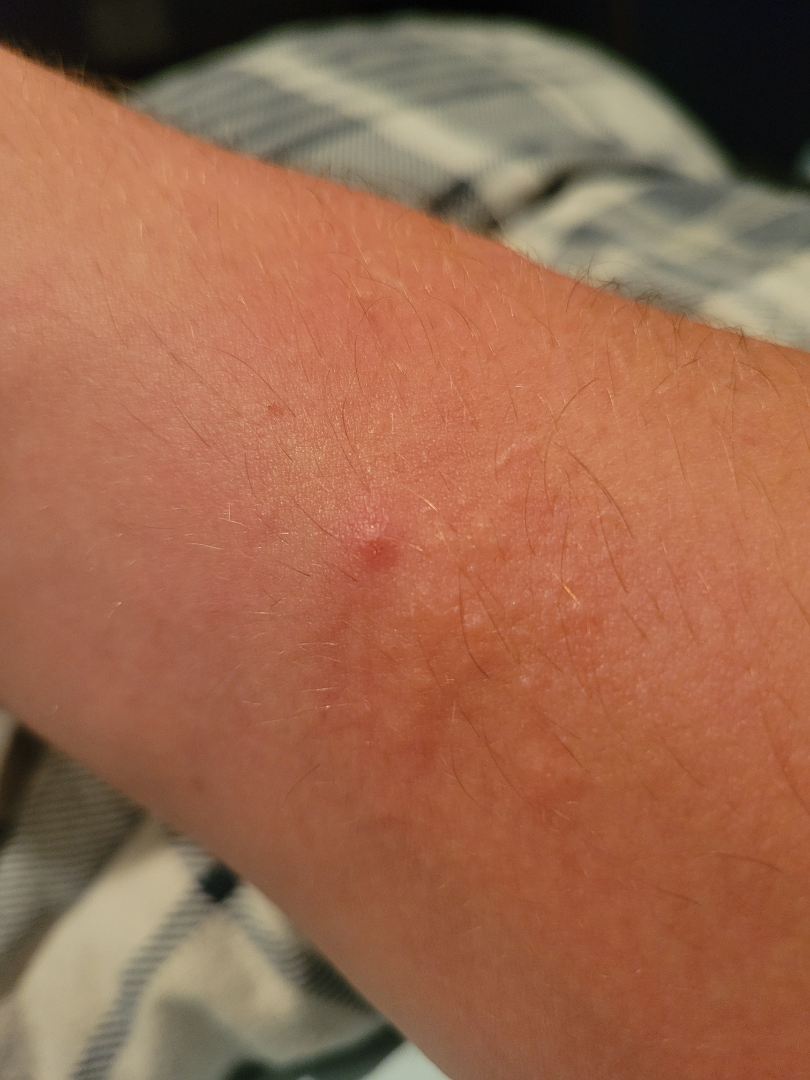Q: What was the assessment?
A: could not be assessed
Q: How does the lesion feel?
A: fluid-filled and raised or bumpy
Q: Where on the body?
A: arm
Q: Constitutional symptoms?
A: joint pain
Q: Reported symptoms?
A: itching
Q: What is the framing?
A: close-up
Q: Duration?
A: less than one week
Q: How does the patient describe it?
A: a rash